A dermatoscopic image of a skin lesion:
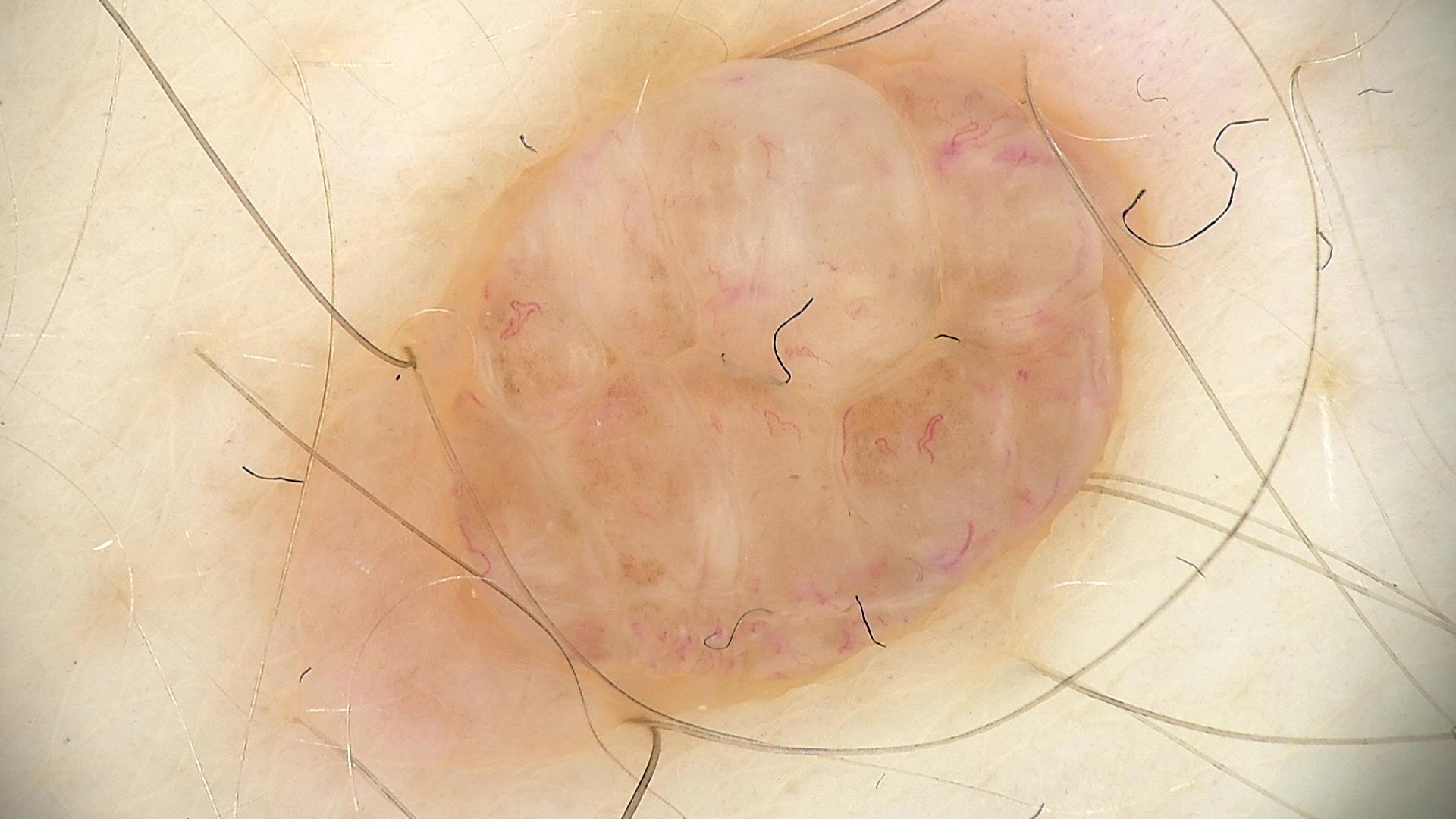Labeled as a banal lesion — a dermal nevus.